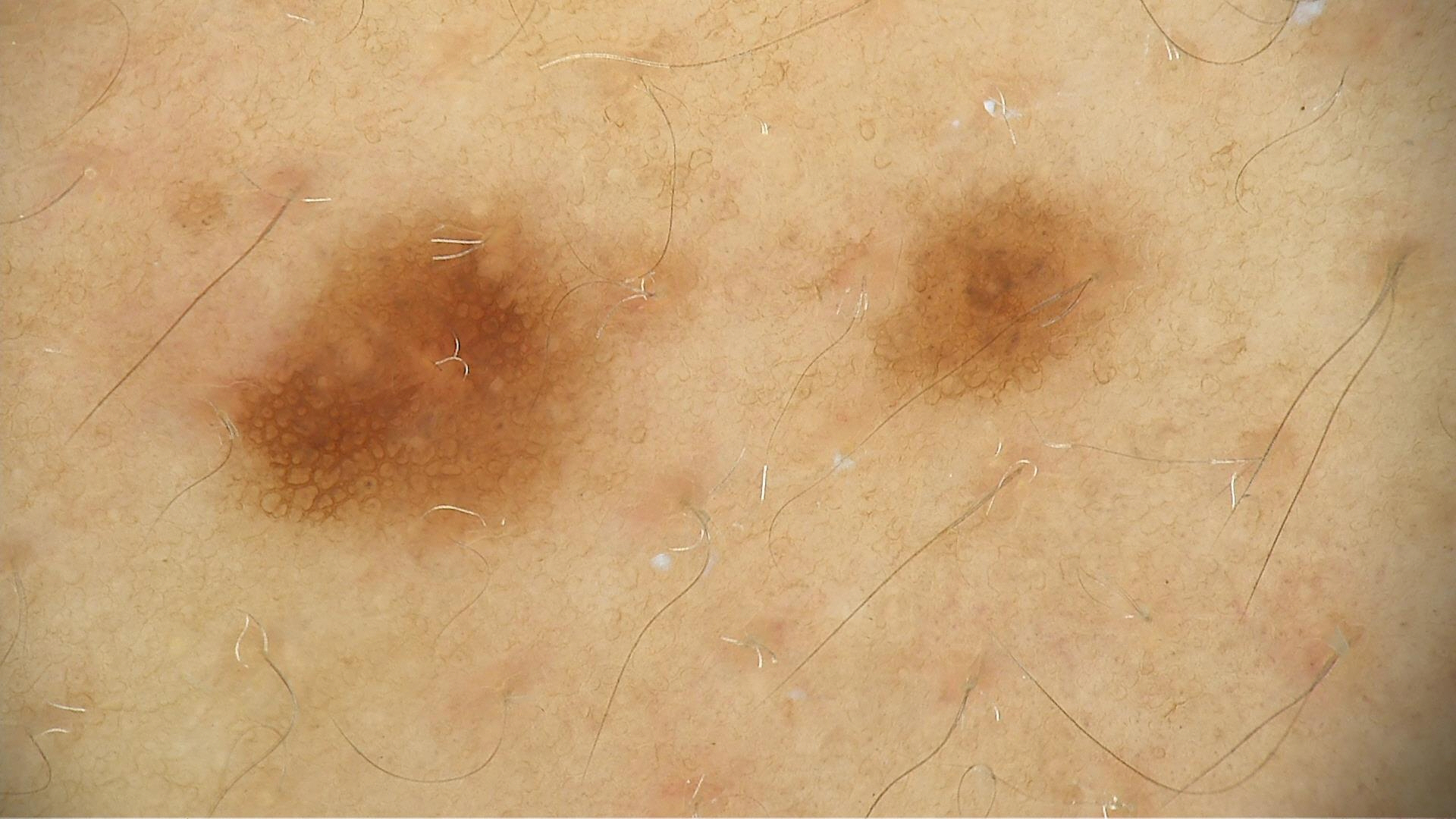Conclusion: Classified as a benign lesion — a dysplastic junctional nevus.